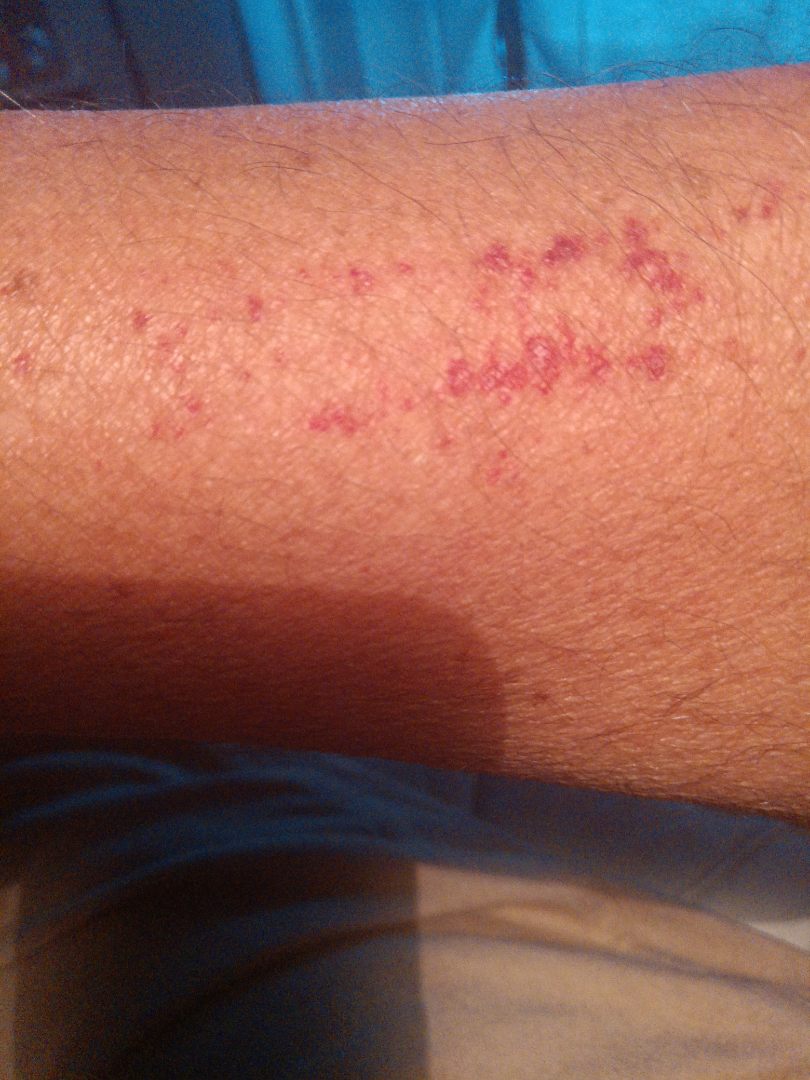assessment: indeterminate; subject: male, age 50–59; shot type: close-up; symptoms: bleeding and itching; described texture: flat; patient describes the issue as: a rash; symptom duration: less than one week; affected area: arm; associated systemic symptoms: none reported; skin tone: FST IV.